This image was taken at an angle · located on the arm: 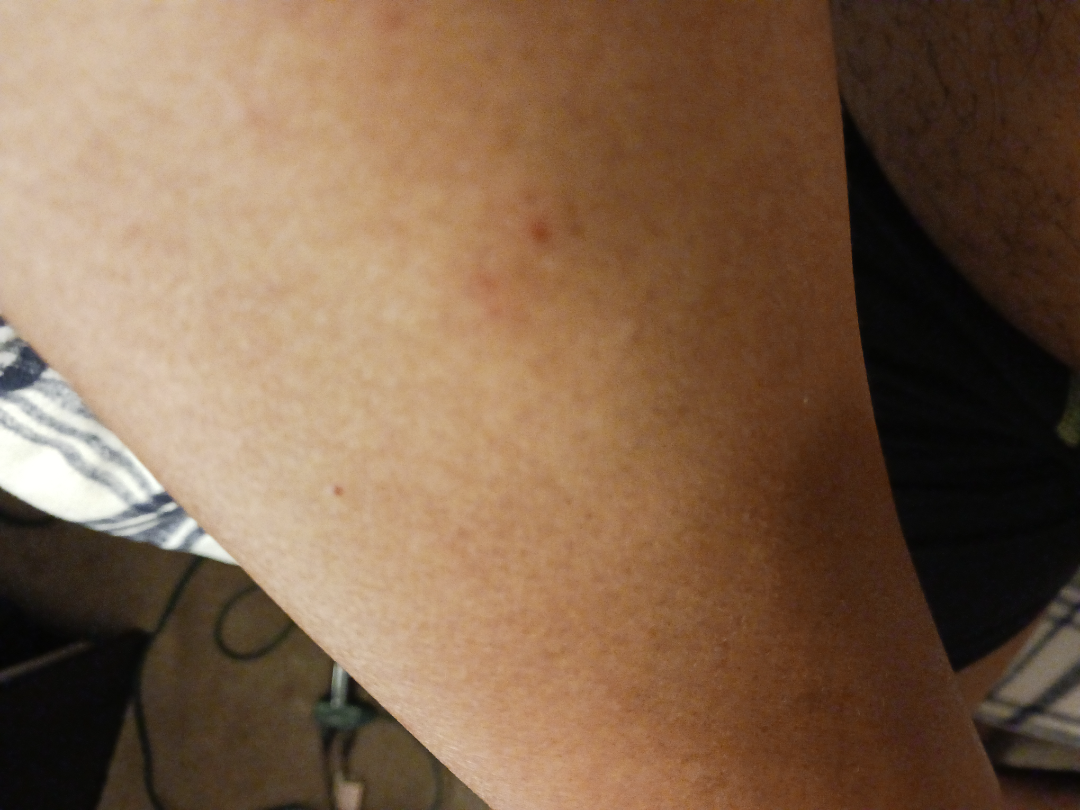Findings:
The skin condition could not be confidently assessed from this image.
Background:
The lesion is associated with itching. No constitutional symptoms were reported. Skin tone: Fitzpatrick IV; lay reviewers estimated Monk Skin Tone 4 or 6 (two reviewer pools disagreed).